A dermoscopy image of a single skin lesion.
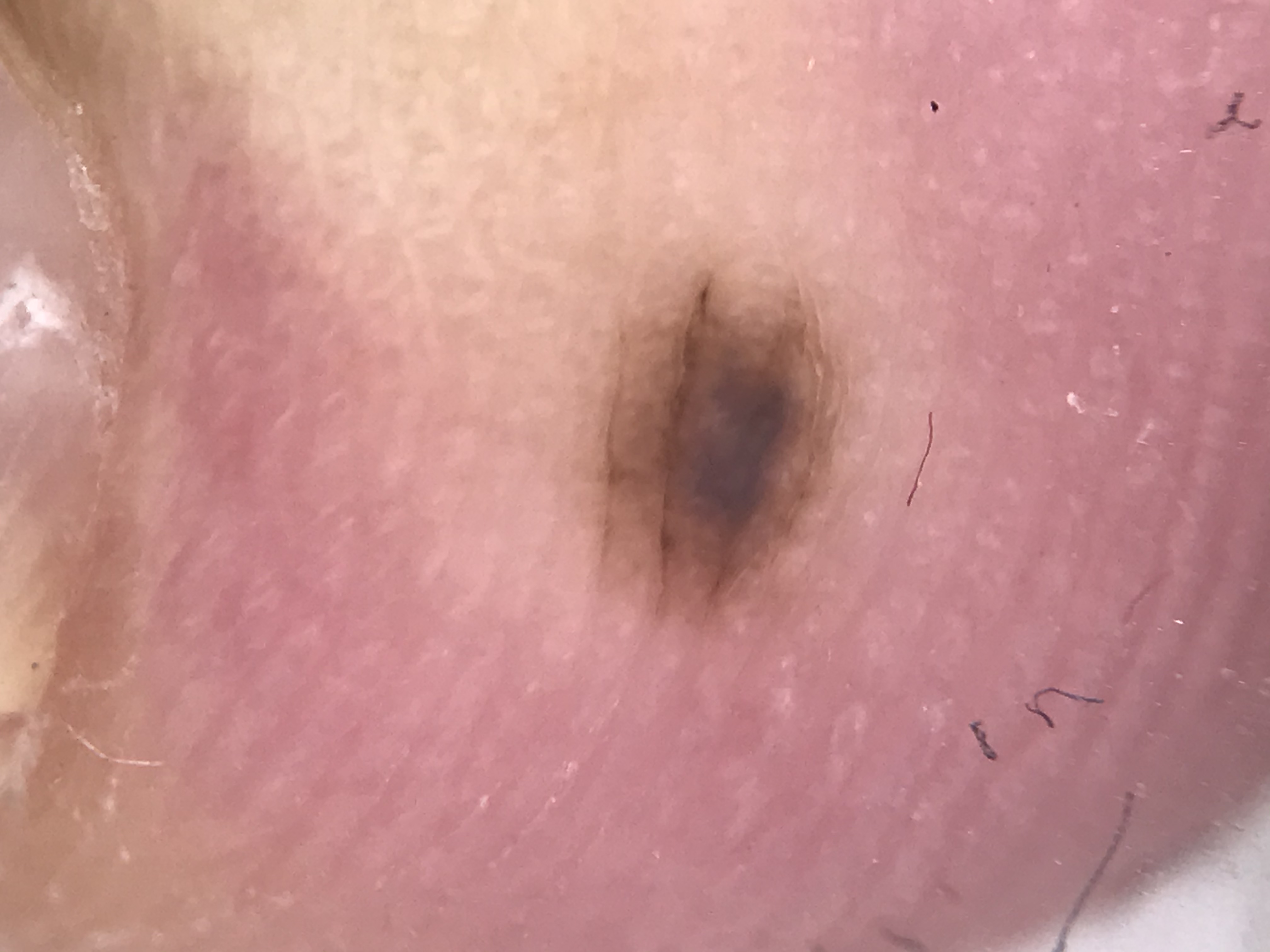The architecture is that of a banal lesion. Consistent with an acral compound nevus.